A dermoscopic photograph of a skin lesion.
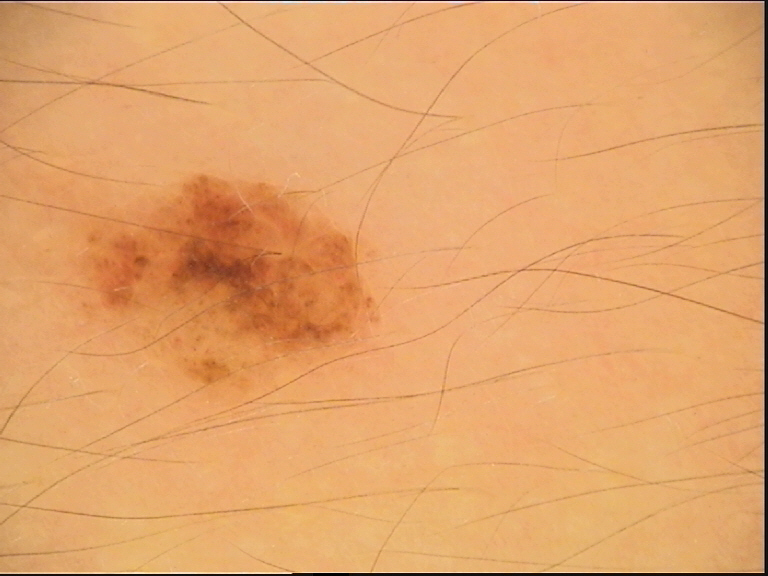{"lesion_type": {"main_class": "banal", "pattern": "compound"}, "diagnosis": {"name": "compound nevus", "code": "cb", "malignancy": "benign", "super_class": "melanocytic", "confirmation": "expert consensus"}}